Skin tone: Fitzpatrick skin type III. A close-up photograph — 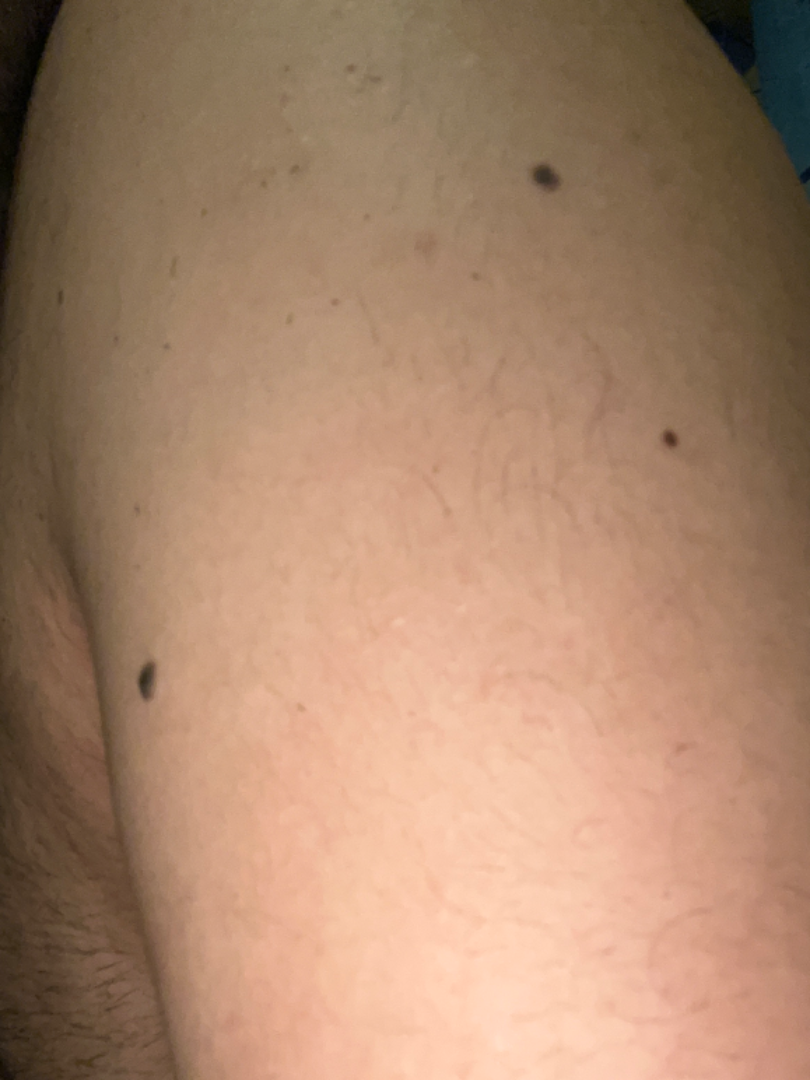Case summary:
– assessment · unable to determine